A skin lesion imaged with a dermatoscope: 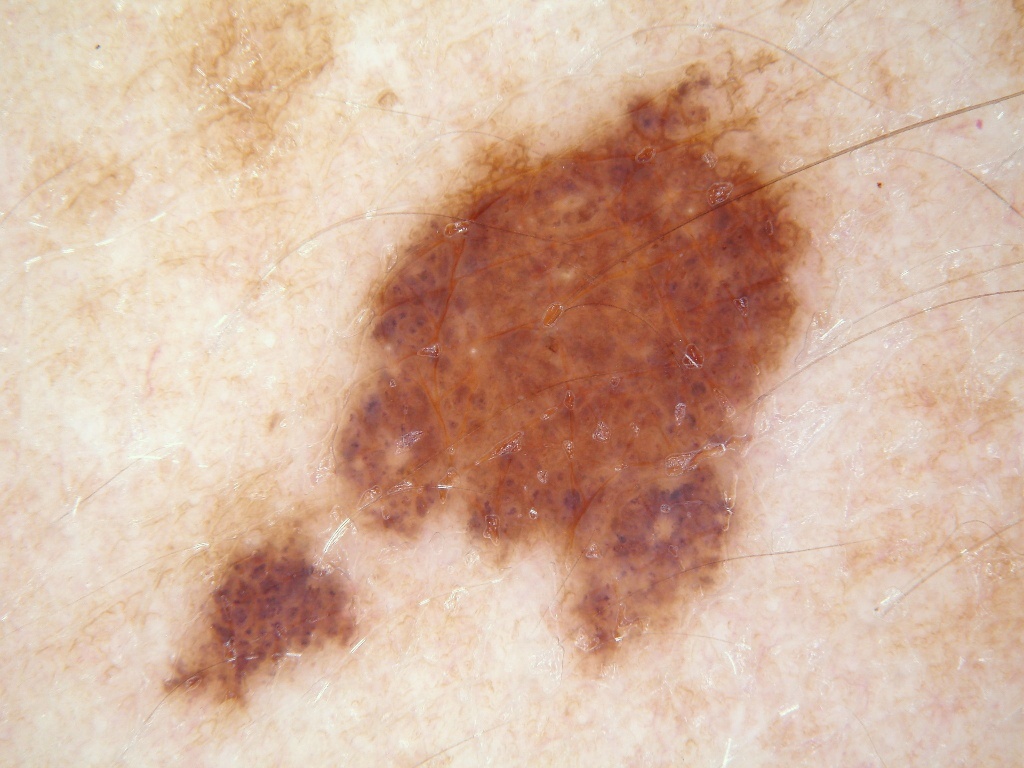{
  "lesion_location": {
    "bbox_xyxy": [
      150,
      38,
      843,
      747
    ]
  },
  "dermoscopic_features": {
    "present": [
      "globules",
      "milia-like cysts",
      "pigment network"
    ],
    "absent": [
      "streaks",
      "negative network"
    ]
  },
  "diagnosis": {
    "name": "melanocytic nevus",
    "malignancy": "benign",
    "lineage": "melanocytic",
    "provenance": "clinical"
  }
}